A dermoscopic image of a skin lesion:
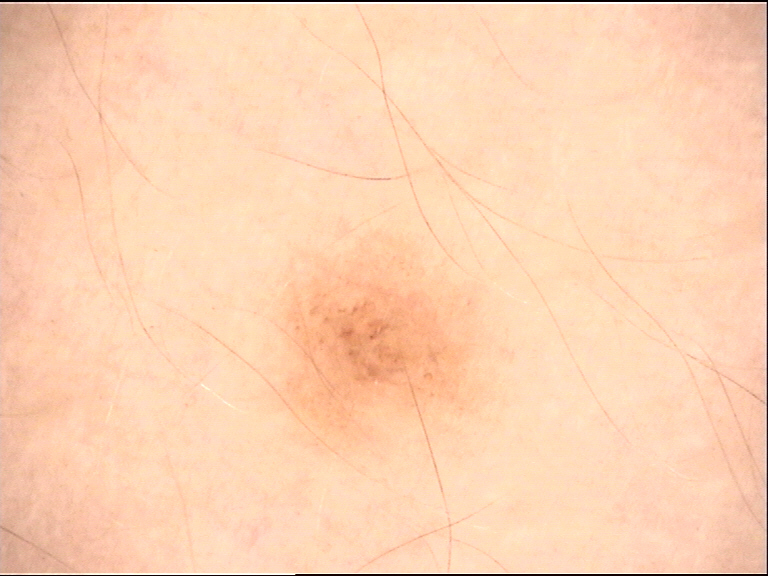Labeled as a banal lesion — a compound nevus.